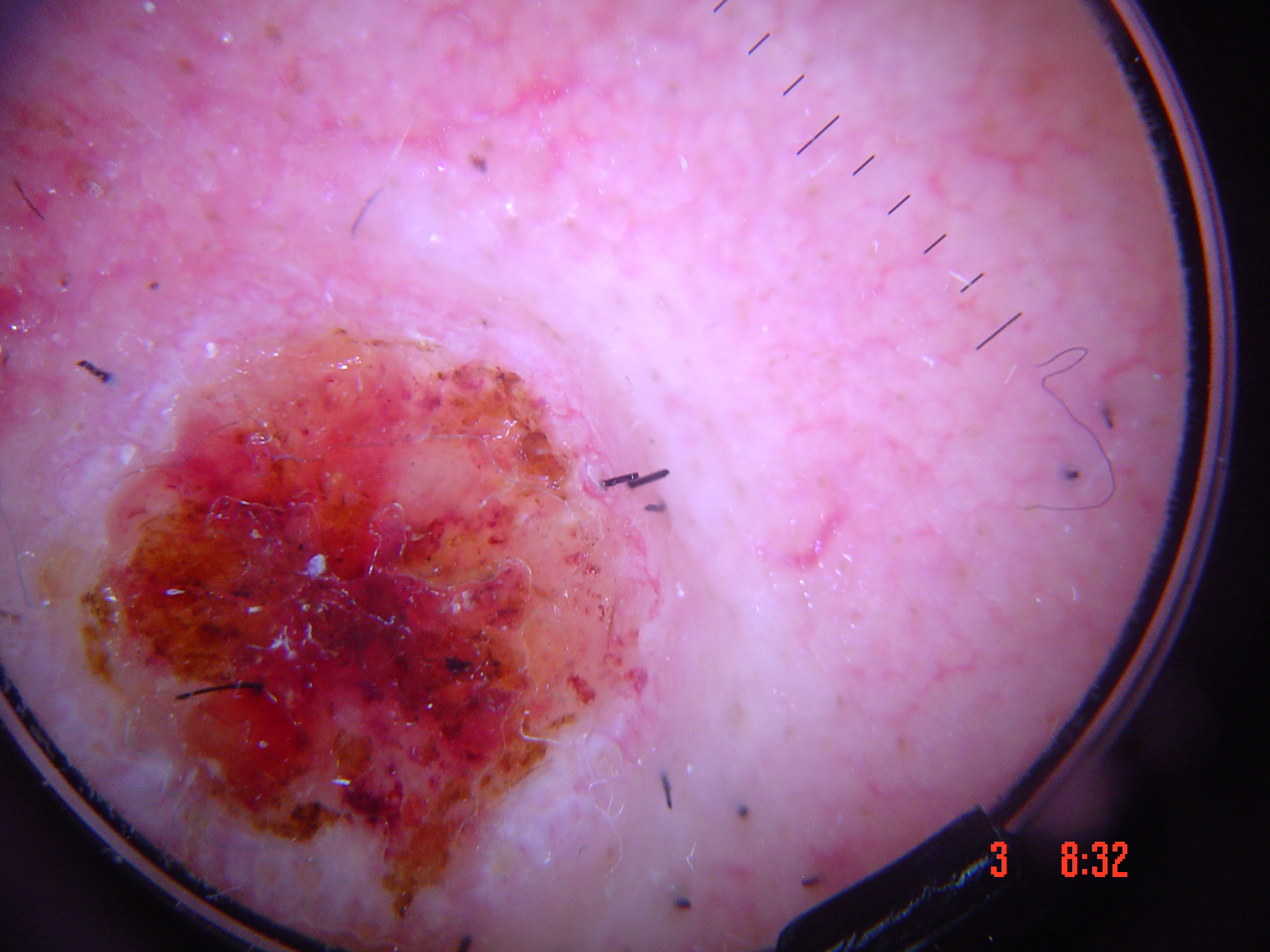Case:
A skin lesion imaged with a dermatoscope.
Diagnosis:
Biopsy-confirmed as a malignant lesion — a squamous cell carcinoma.